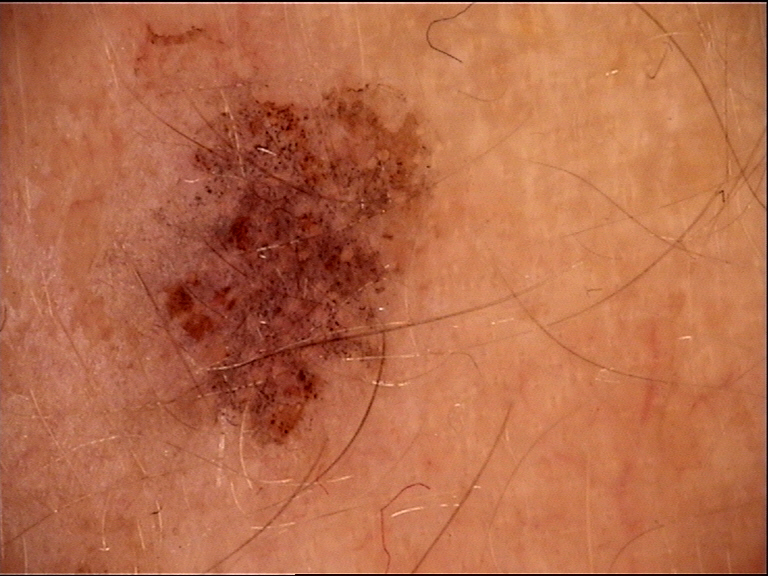diagnosis — lichenoid keratosis (expert consensus).